The photograph is a close-up of the affected area · the subject is 30–39, female · self-categorized by the patient as skin that appeared healthy to them · the condition has been present for one to four weeks · symptoms reported: itching and bothersome appearance · the affected area is the leg — 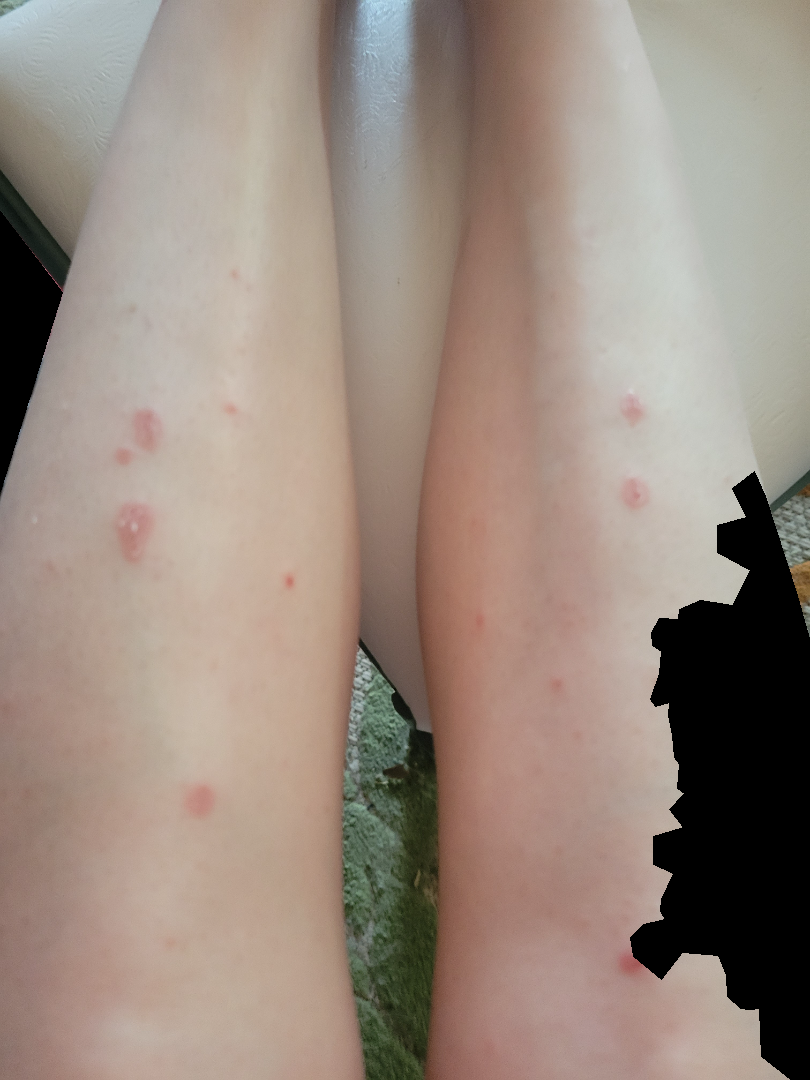{
  "differential": {
    "leading": [
      "Psoriasis"
    ],
    "unlikely": [
      "Eczema",
      "Drug Rash",
      "Pityriasis lichenoides",
      "Lichen planus/lichenoid eruption"
    ]
  }
}